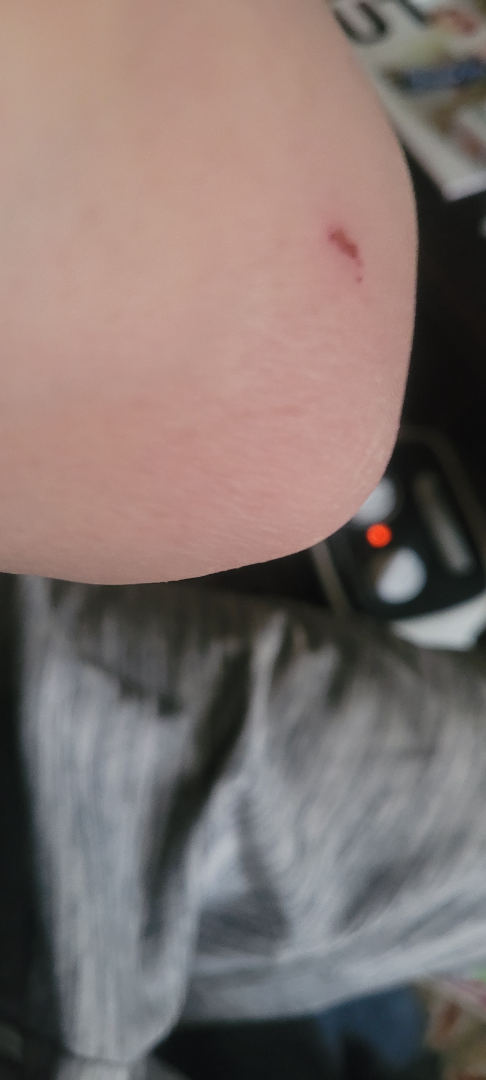Patient information:
The affected area is the arm. The subject is male. The lesion is described as rough or flaky. The condition has been present for more than one year. This is a close-up image.
Review:
Abrasion, scrape, or scab (possible); Inflicted skin lesions (possible).